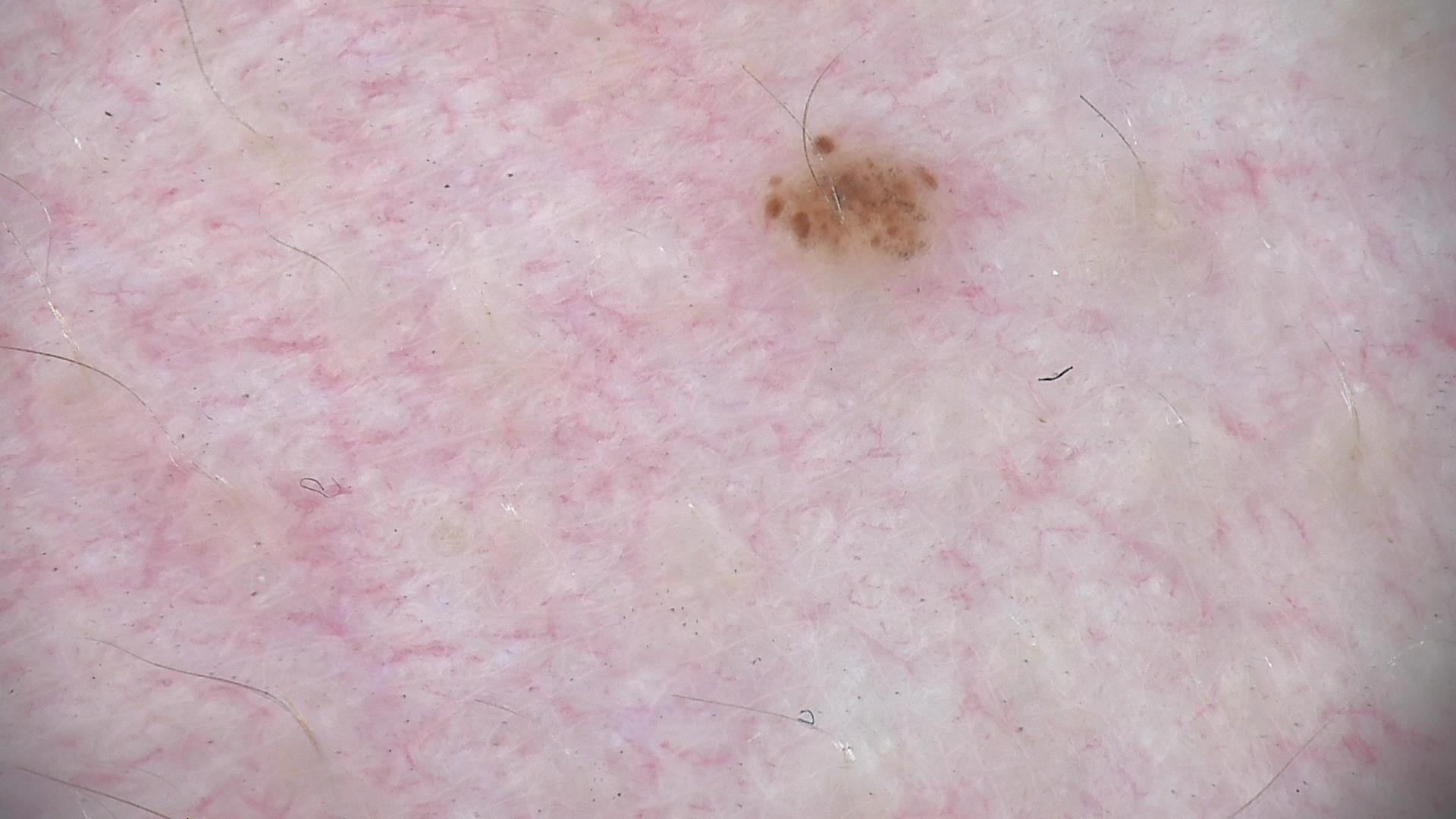Q: What is this lesion?
A: dysplastic junctional nevus (expert consensus)